A dermoscopic image of a skin lesion: 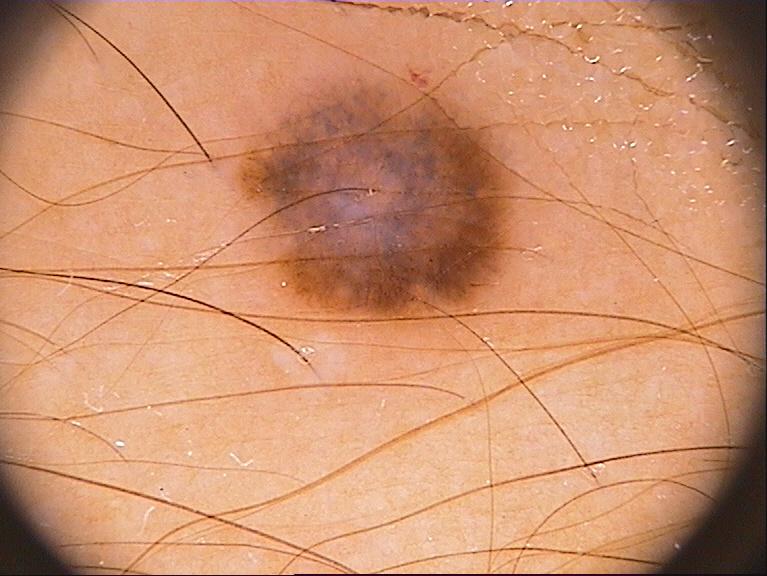With coordinates (x1, y1, x2, y2), the visible lesion spans [227, 74, 530, 329]. The lesion takes up about 14% of the image. The diagnostic assessment was a benign lesion.